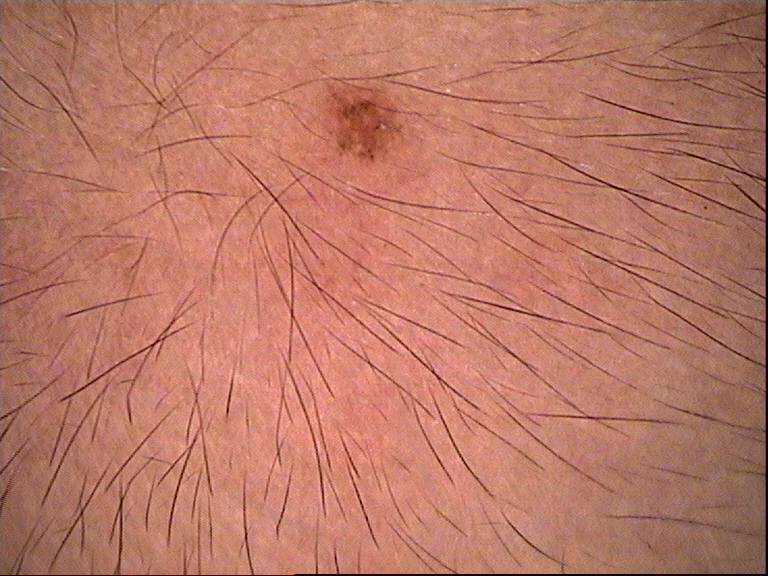Summary:
A dermoscopic image of a skin lesion.
Conclusion:
Consistent with a compound lesion — a Miescher nevus.